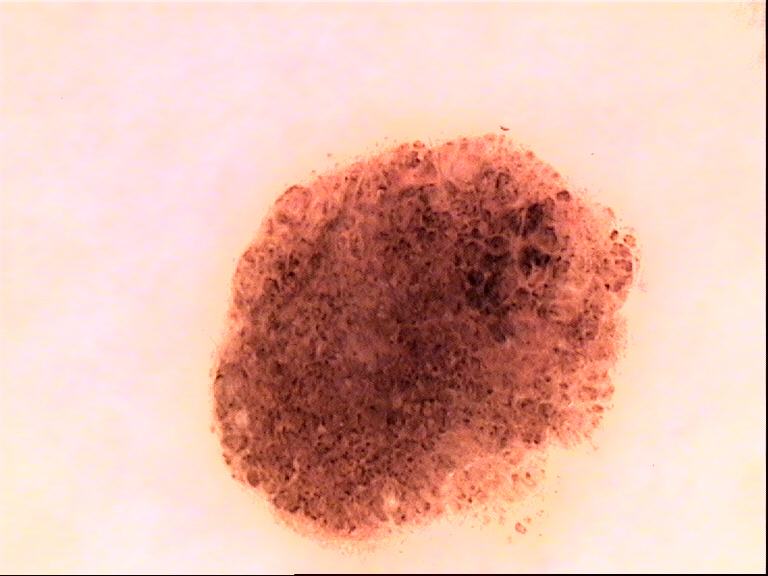diagnosis:
  name: dysplastic compound nevus
  code: cd
  malignancy: benign
  super_class: melanocytic
  confirmation: expert consensus